A dermoscopic image of a skin lesion.
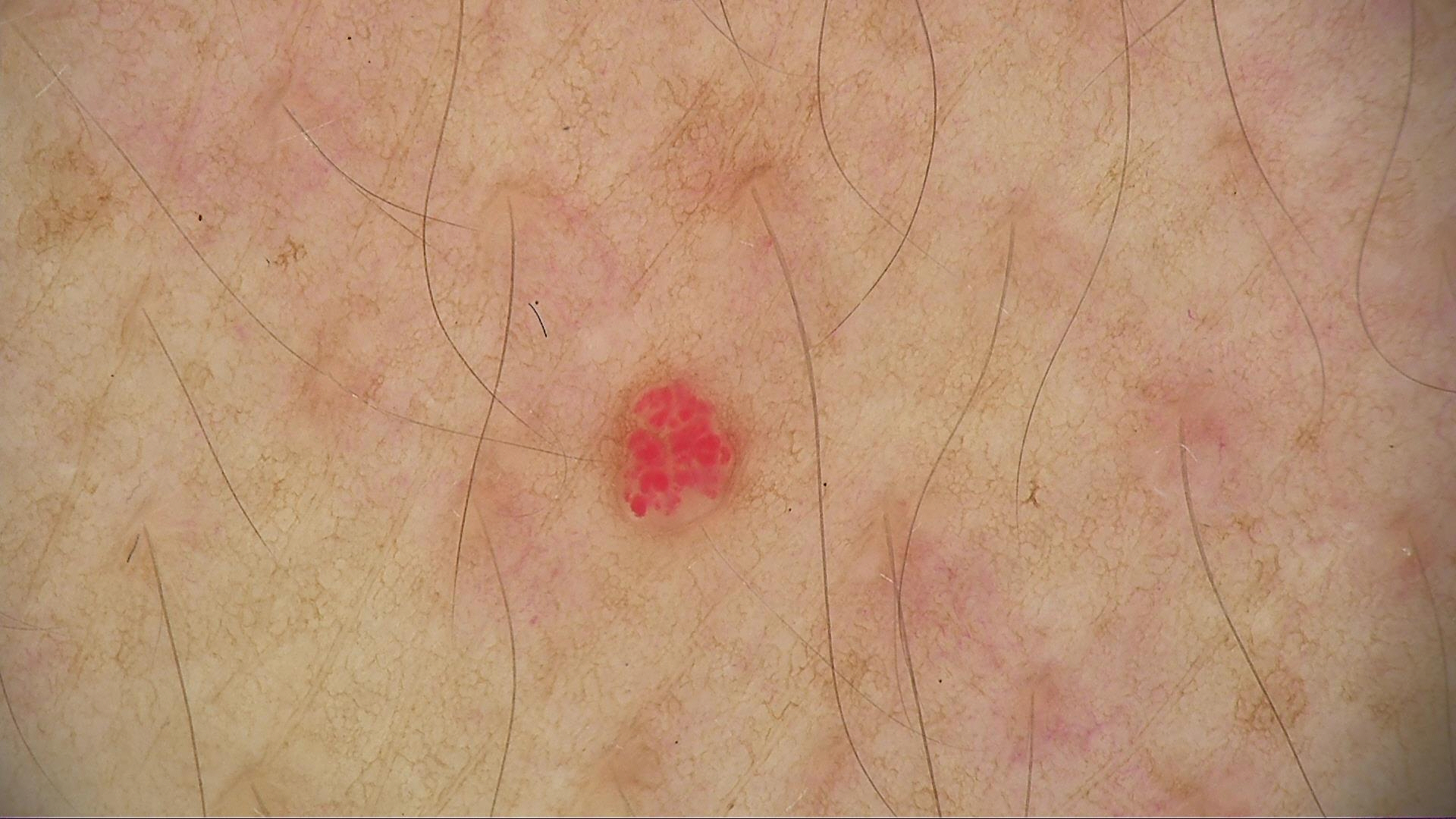The architecture is that of a vascular lesion.
Labeled as a hemangioma.